A dermatoscopic image of a skin lesion.
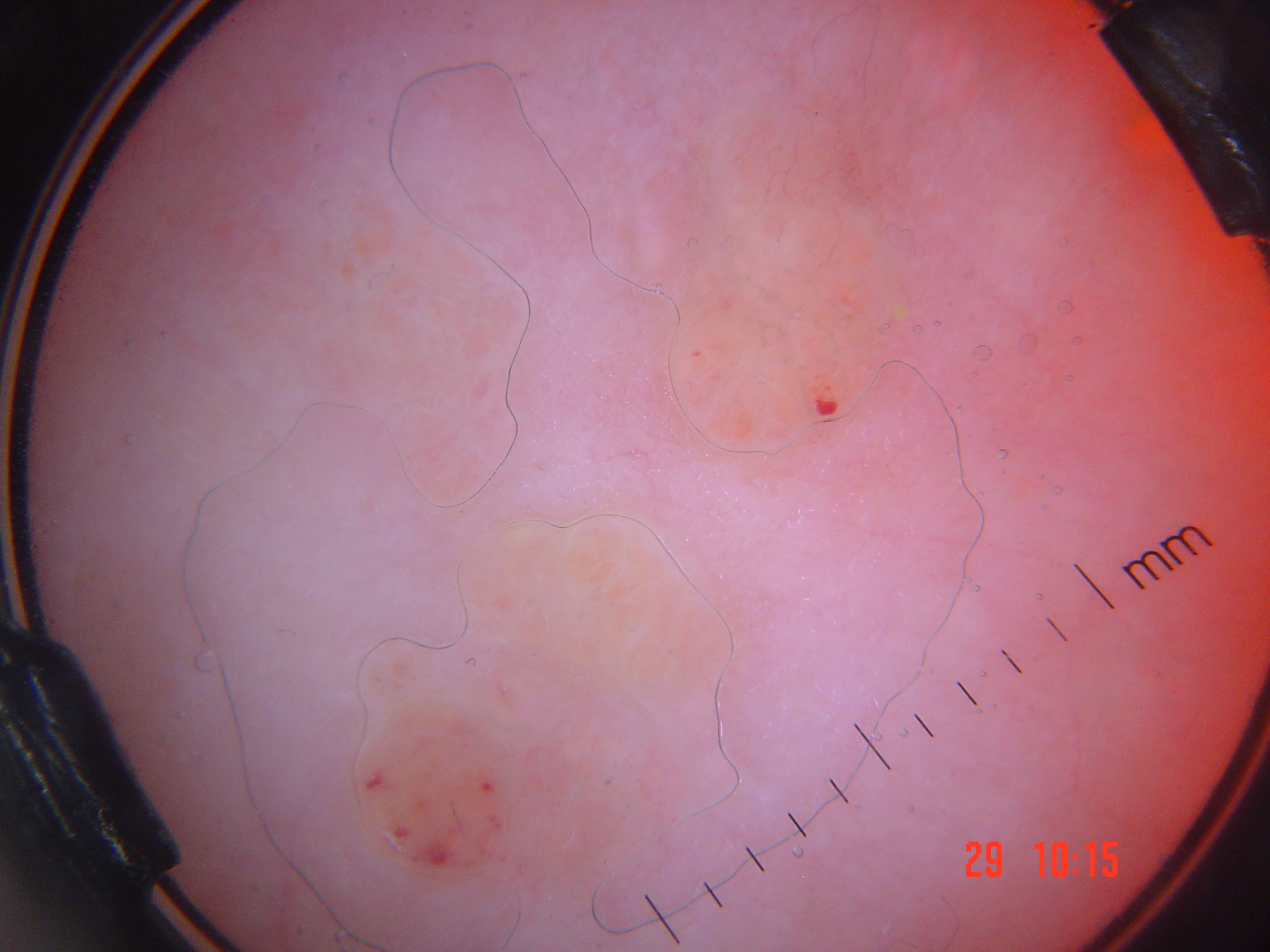The architecture is that of a vascular lesion.
Classified as a lymphangioma.